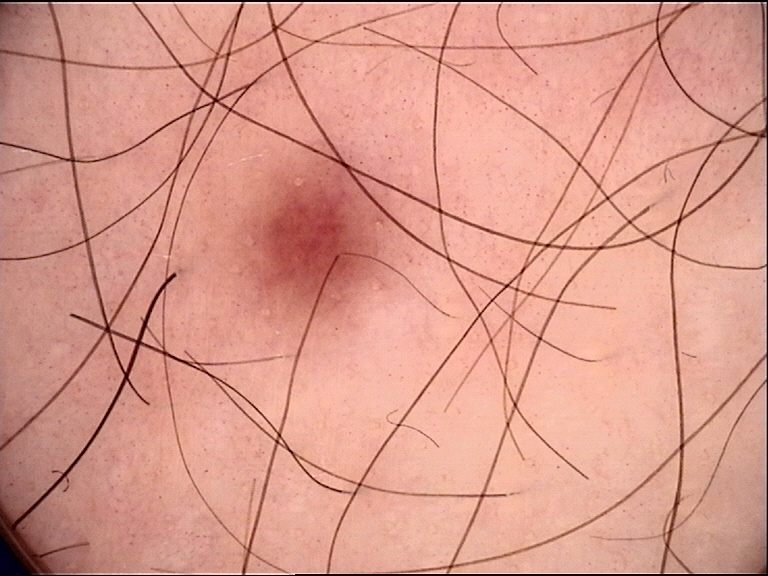Summary: A dermatoscopic image of a skin lesion. The morphology is that of a banal lesion. Impression: Classified as a junctional nevus.